The affected area is the arm; a close-up photograph: 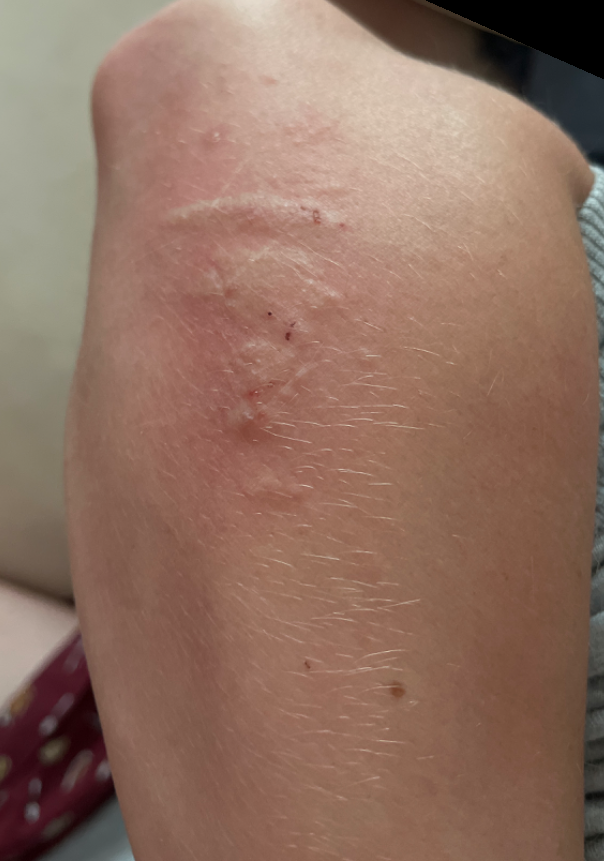impression=a single dermatologist reviewed the case: in keeping with Urticaria.